A moderate number of moles by the patient's own estimate; a female subject 81 years old; acquired for a research image collection, with no referral diagnosis; the patient says their skin reddens painfully with sun exposure; a clinical photograph of a skin lesion — 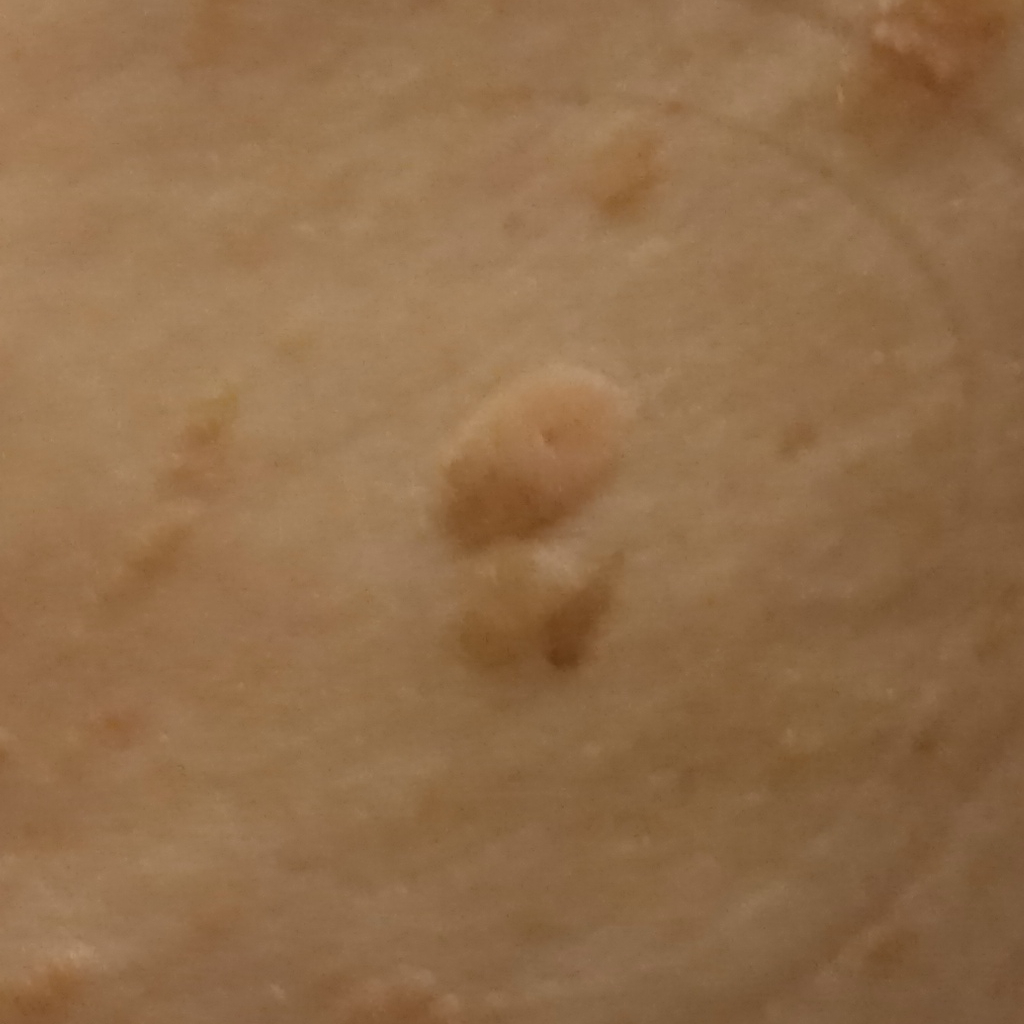Q: What is the anatomic site?
A: the back
Q: Lesion size?
A: 15.5 mm
Q: What was the diagnosis?
A: seborrheic keratosis (dermatologist consensus)